Dermoscopy of a skin lesion — 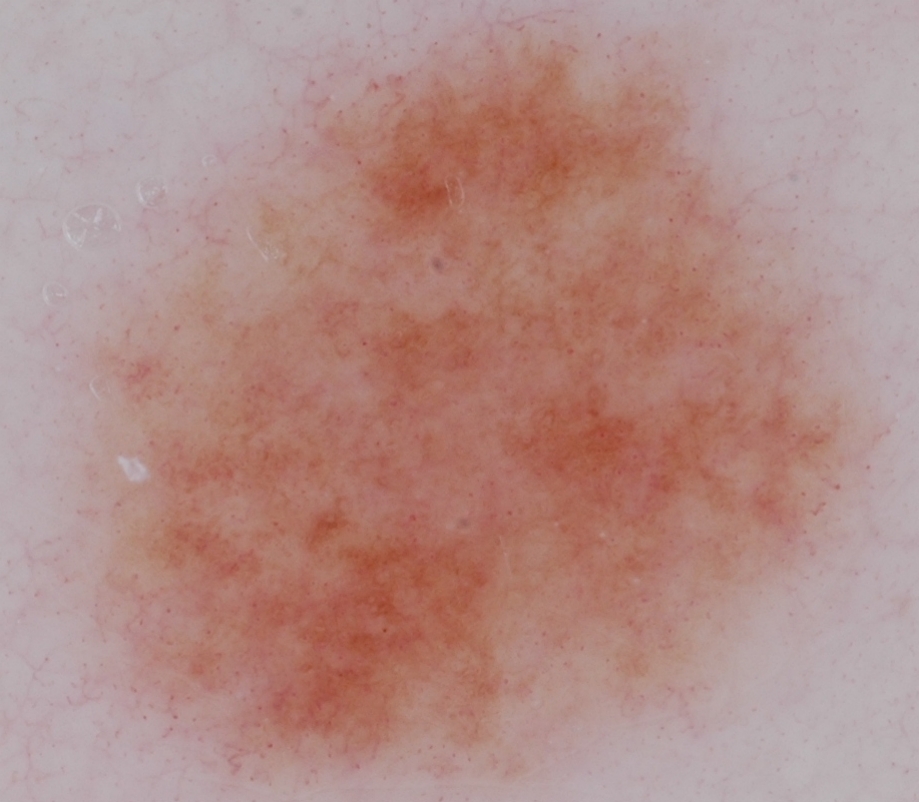Case summary:
Dermoscopy demonstrates globules; no pigment network, negative network, streaks, or milia-like cysts. The lesion reaches across nearly the entire image.
Impression:
Expert review diagnosed this as a melanocytic nevus, a benign lesion.